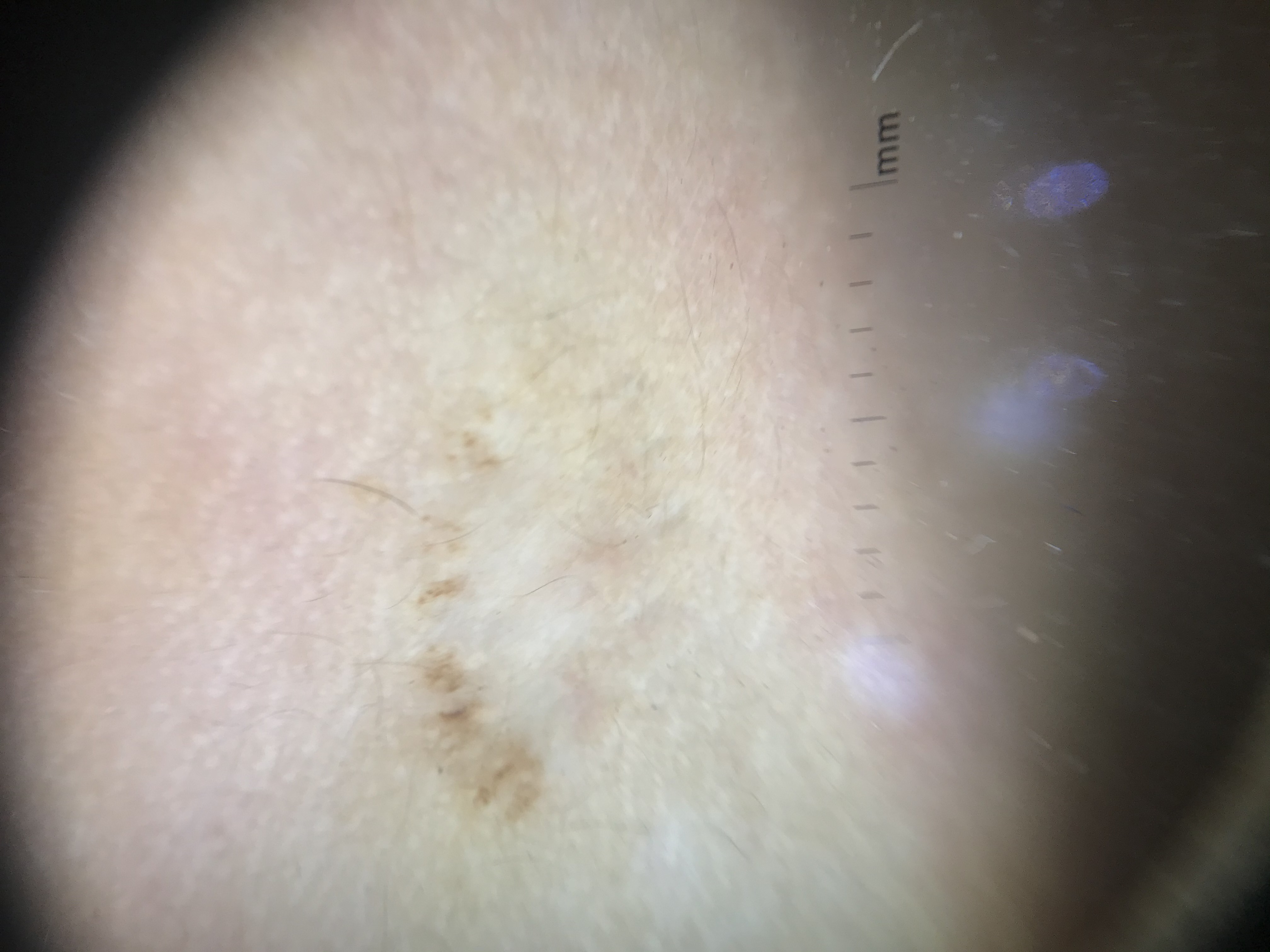Case:
* diagnosis — recurrent nevus (expert consensus)